The back of the hand is involved · the contributor is a female aged 50–59 · the photo was captured at an angle.
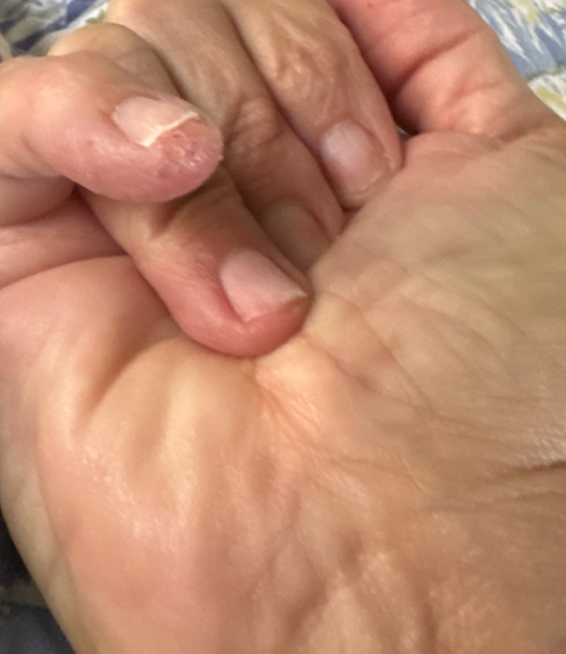The contributor reports the condition has been present for one to three months. Self-categorized by the patient as a rash. Skin tone: FST IV. The reviewing dermatologist's impression was: consistent with Acute-on-chronic dyshidrotic eczema of hands.